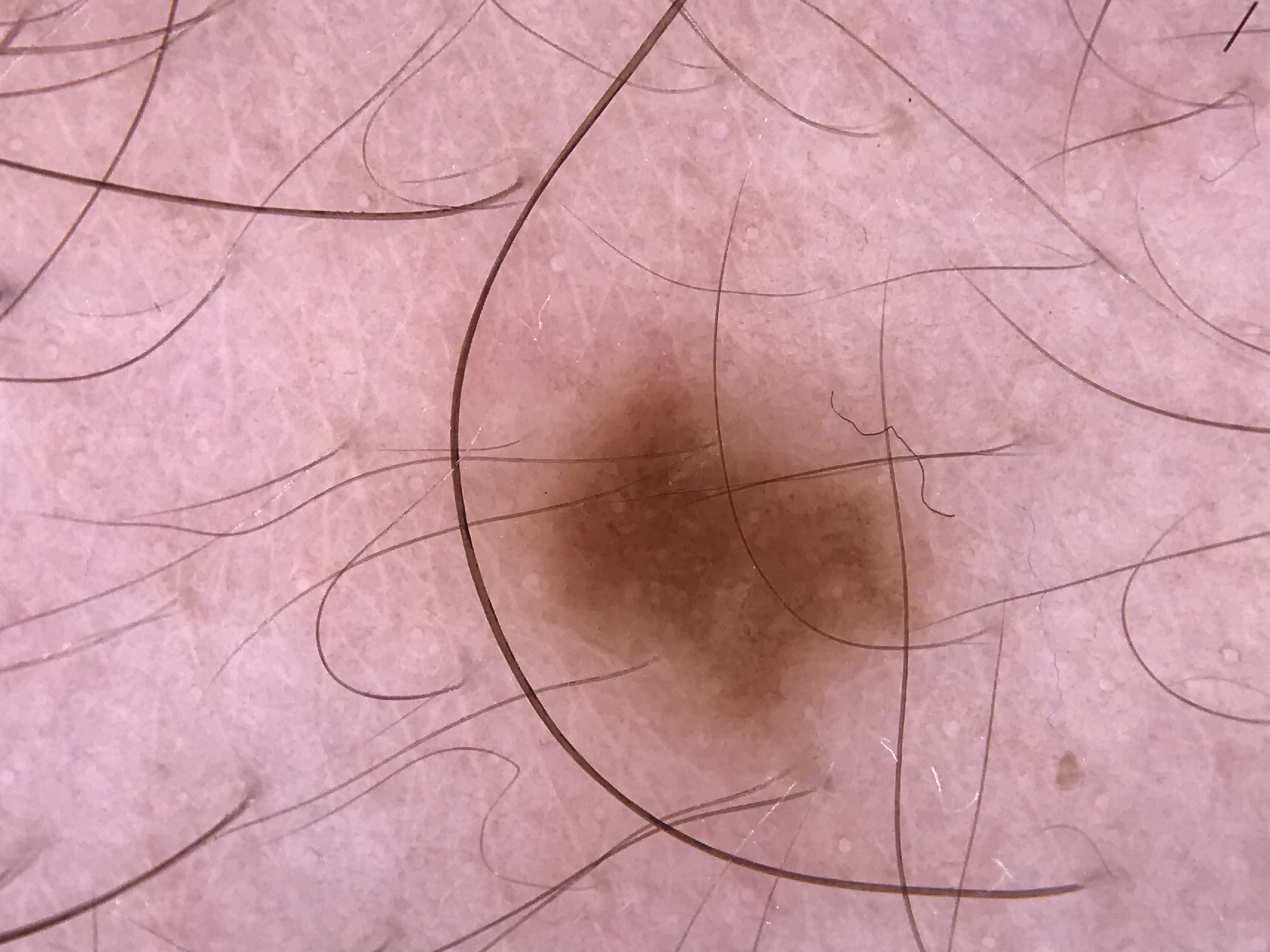{
  "image": "dermoscopy",
  "lesion_type": {
    "main_class": "banal",
    "pattern": "junctional"
  },
  "diagnosis": {
    "name": "junctional nevus",
    "code": "jb",
    "malignancy": "benign",
    "super_class": "melanocytic",
    "confirmation": "expert consensus"
  }
}